A smartphone photograph of a skin lesion — 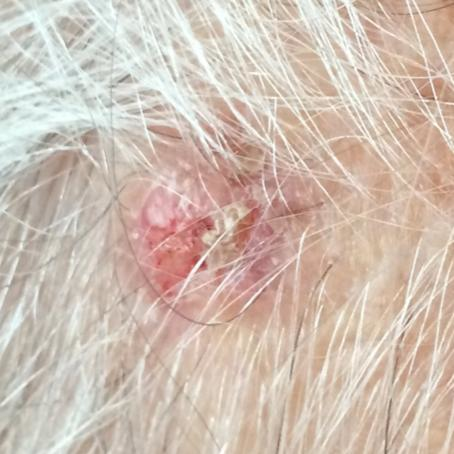{"lesion_location": "the face", "symptoms": {"present": ["itching", "growth", "pain", "elevation"]}, "diagnosis": {"name": "basal cell carcinoma", "code": "BCC", "malignancy": "malignant", "confirmation": "histopathology"}}